Collected as part of a research study, without a referral diagnosis; a dermatoscopic image of a skin lesion; the patient says their skin tans without first burning; few moles overall by the patient's own estimate; a female subject age 67: 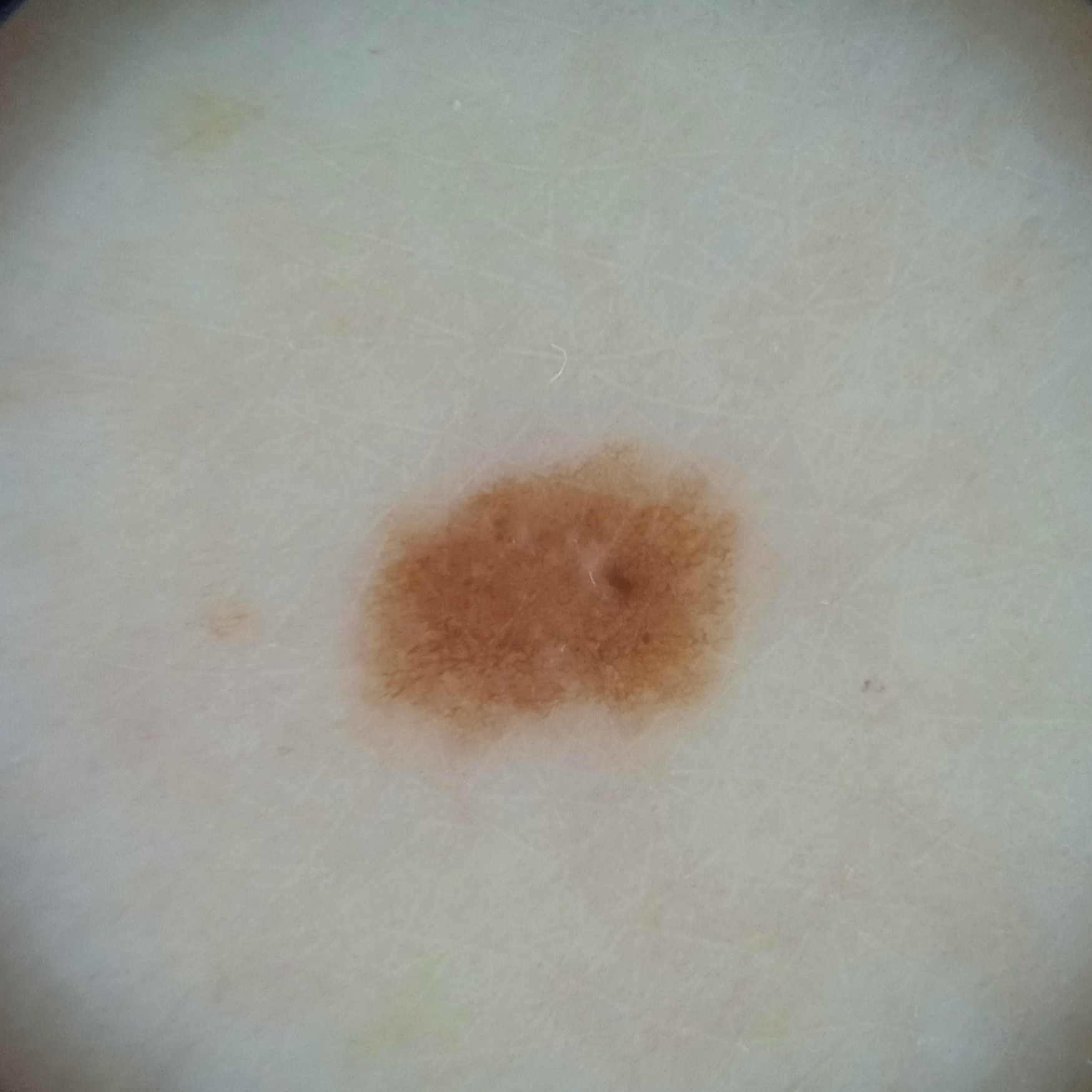The lesion is about 4.9 mm across.
The dermatologists' assessment was a melanocytic nevus.